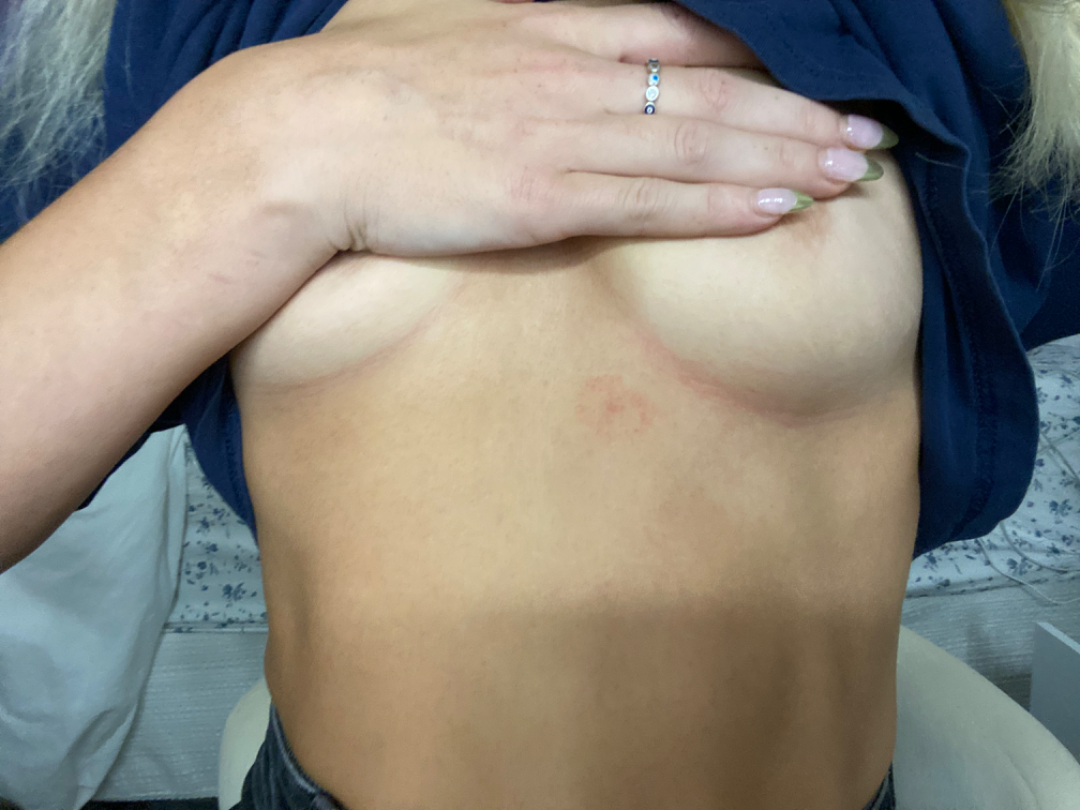{"duration": "about one day", "symptoms": "bothersome appearance", "shot_type": "at a distance", "body_site": "front of the torso", "differential": {"leading": ["Tinea"], "considered": ["Eczema", "Irritant Contact Dermatitis"]}}